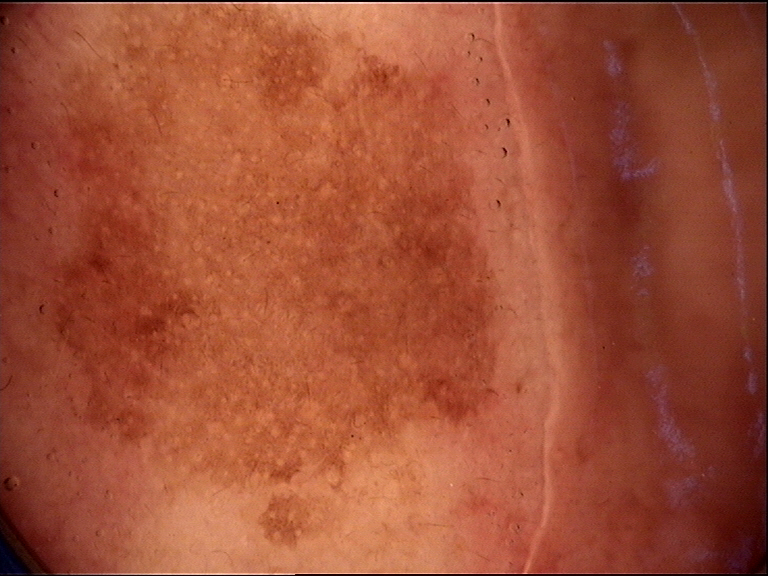image = dermoscopy; subtype = keratinocytic; label = seborrheic keratosis (expert consensus).